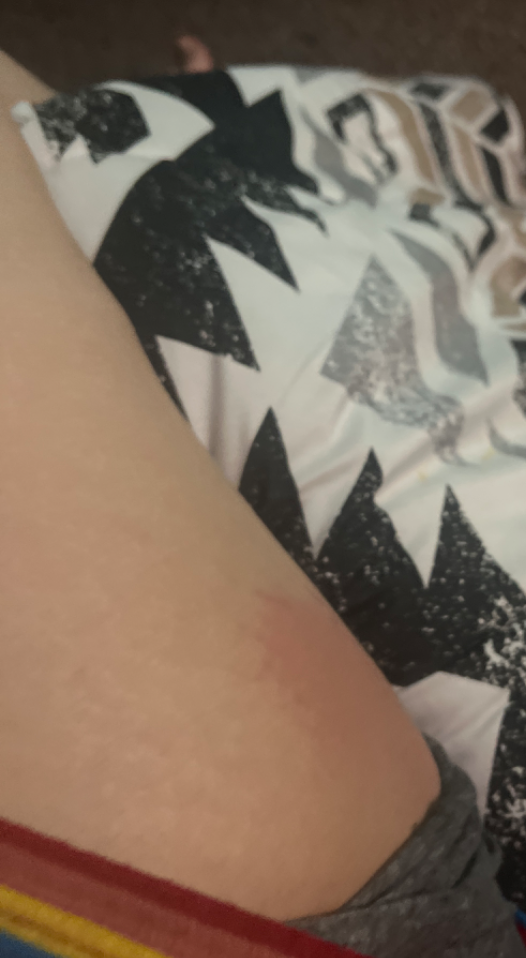The skin condition could not be confidently assessed from this image. Texture is reported as flat. The patient indicates the condition has been present for about one day. Symptoms reported: burning and pain. The lesion involves the leg. The photograph was taken at a distance. The patient considered this a rash.